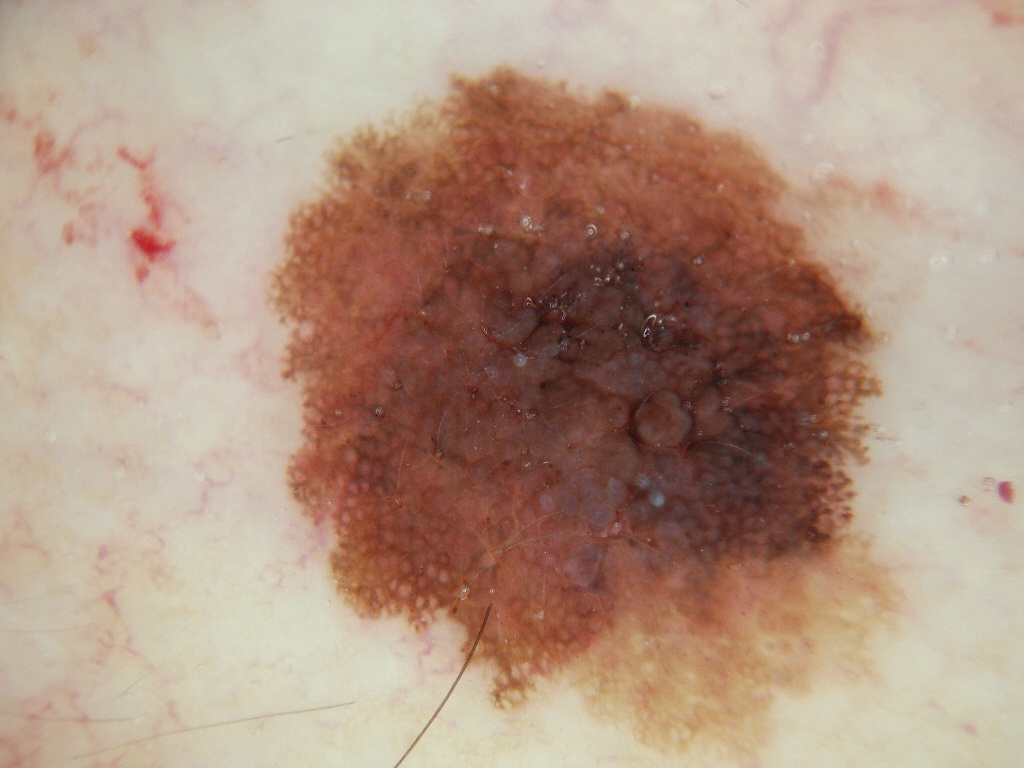The subject is a female aged 48 to 52. A dermoscopic image of a skin lesion. In (x1, y1, x2, y2) order, the lesion's extent is 252 62 930 752. The lesion takes up about 42% of the image. The dermoscopic pattern shows pigment network, globules, and streaks; no milia-like cysts or negative network. The clinical diagnosis was a melanocytic nevus.